A dermoscopic close-up of a skin lesion:
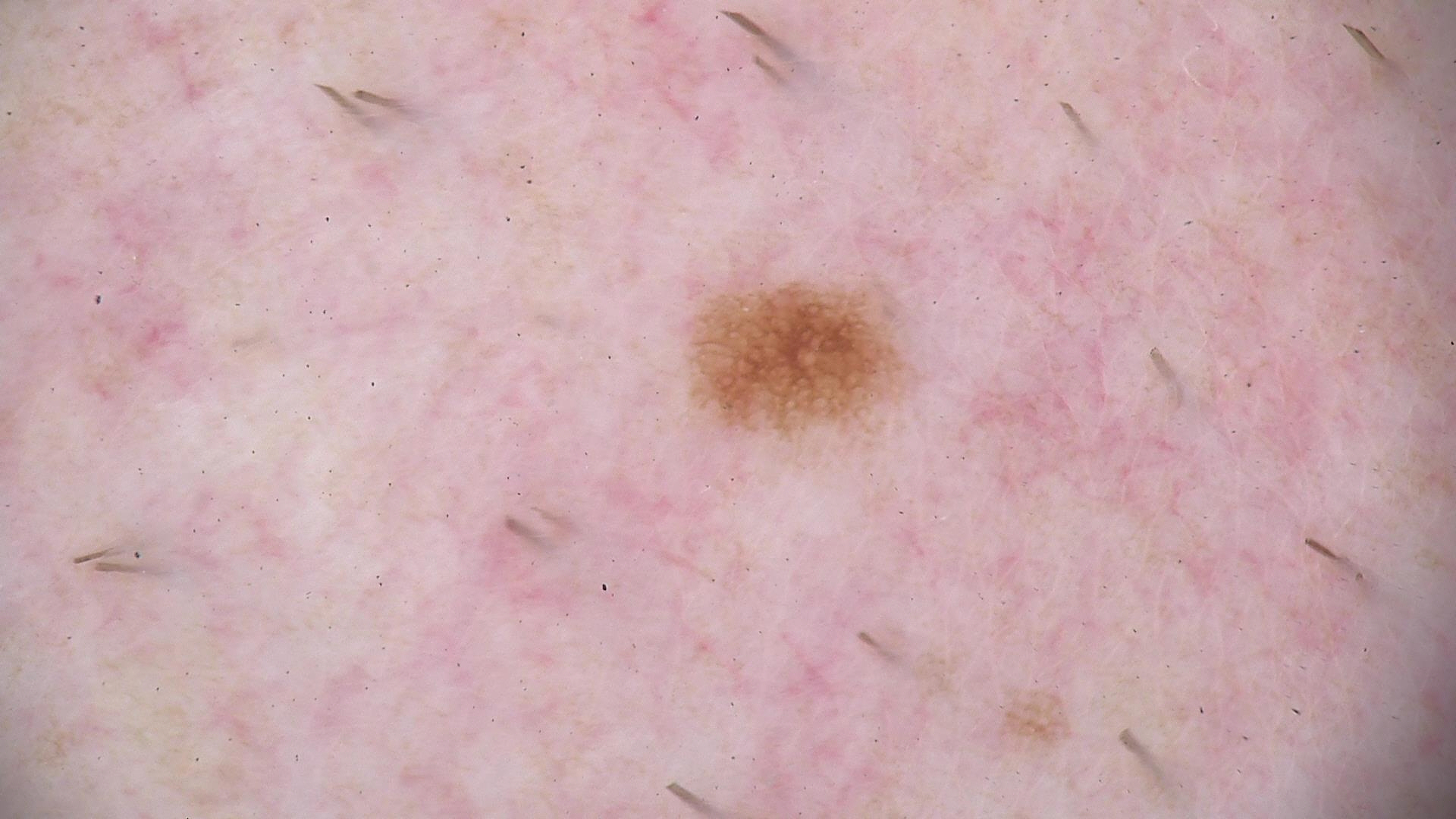Findings:
- assessment · dysplastic junctional nevus (expert consensus)